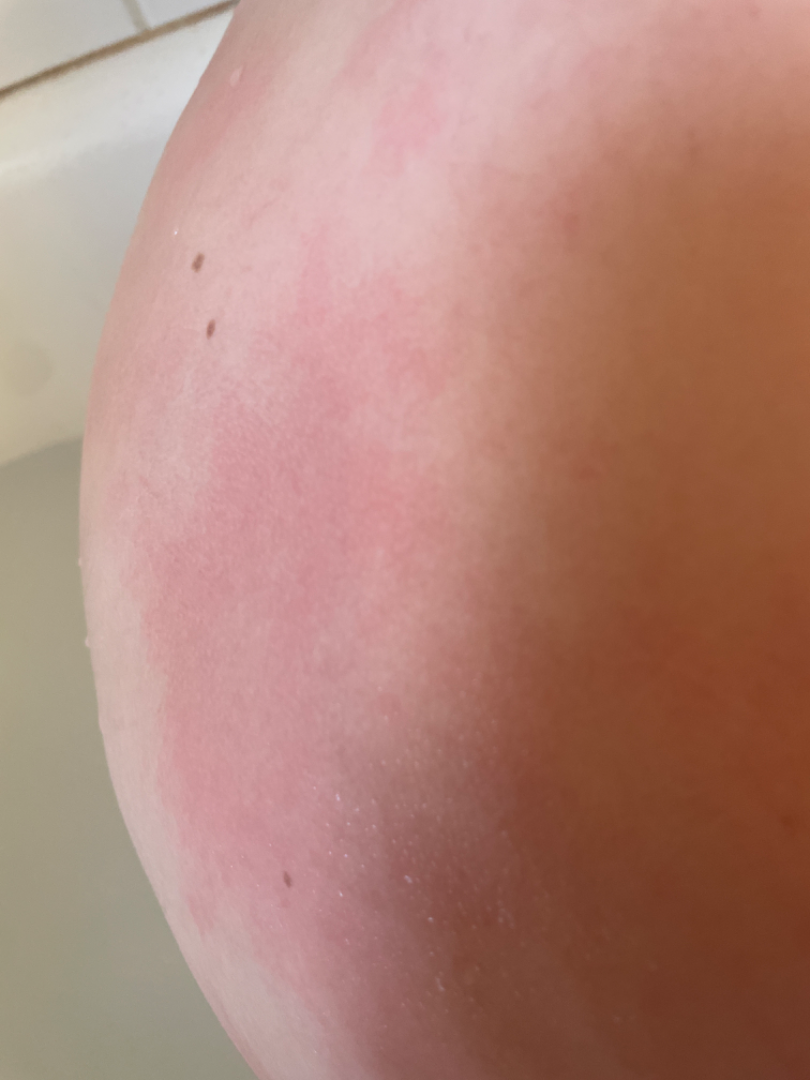shot_type: at an angle
patient_category: a rash
body_site:
  - head or neck
  - front of the torso
  - back of the torso
symptoms: itching
patient: female, age 18–29
duration: about one day
texture: flat
differential:
  tied_lead:
    - Hypersensitivity
    - Allergic Contact Dermatitis